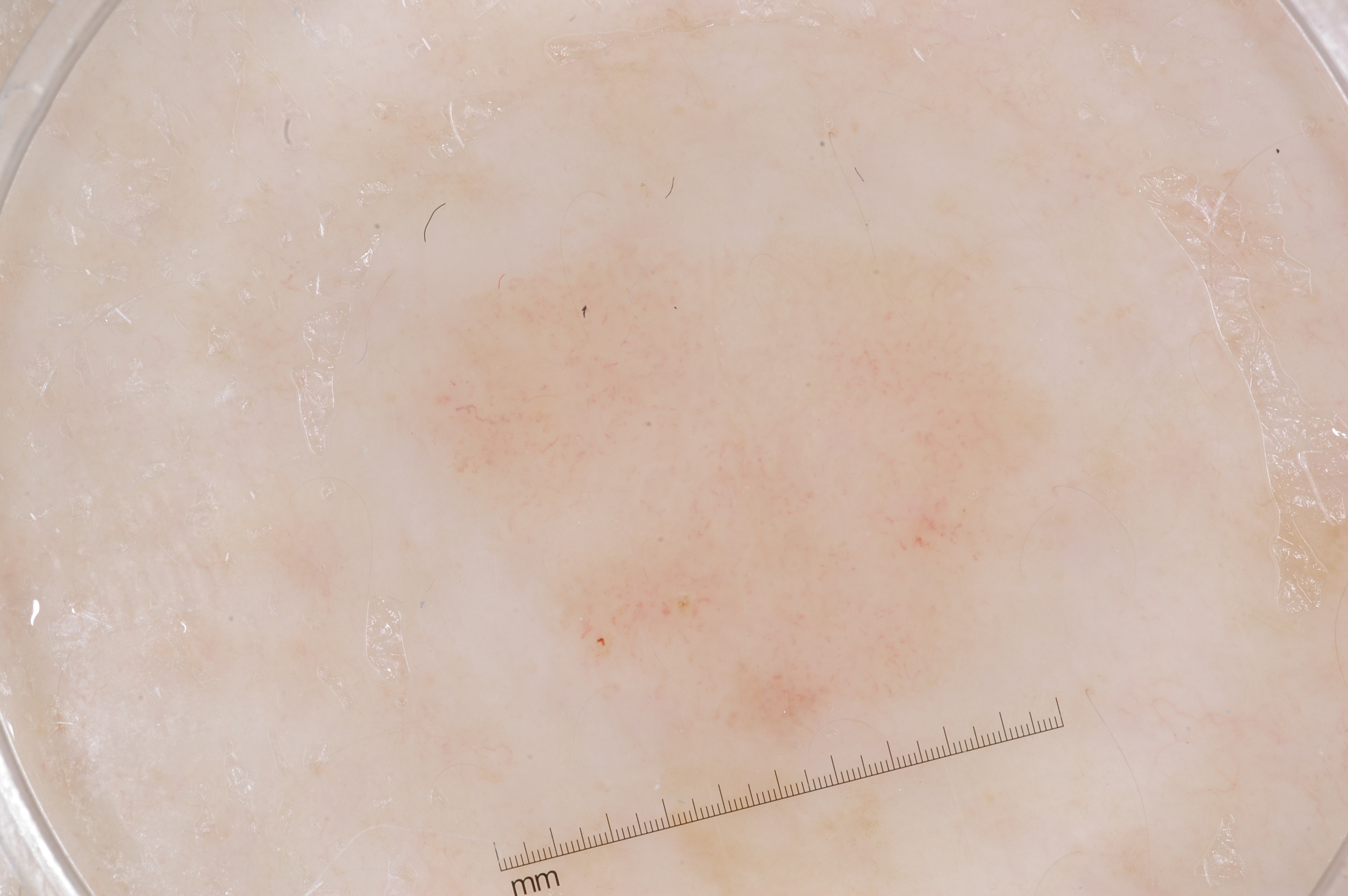Image and clinical context: A female subject about 60 years old. A dermoscopy image of a single skin lesion. As (left, top, right, bottom), the lesion spans box(399, 213, 1069, 781). The lesion covers approximately 25% of the dermoscopic field. The dermoscopic pattern shows no streaks, pigment network, milia-like cysts, or negative network. Assessment: Expert review diagnosed this as a seborrheic keratosis, a benign skin lesion.